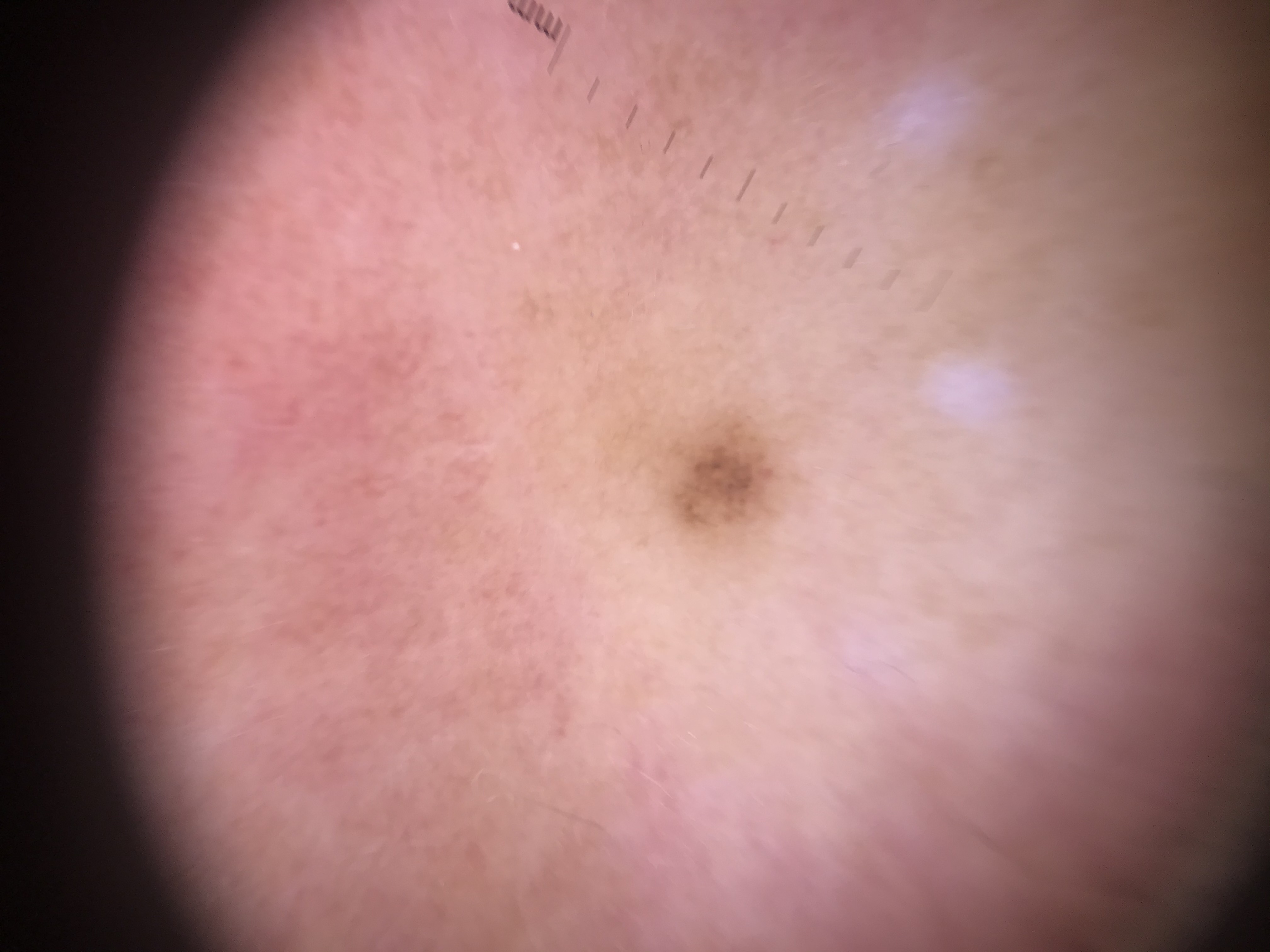Classified as a banal lesion — a junctional nevus.